No relevant systemic symptoms · the front of the torso is involved · FST II · the lesion is described as raised or bumpy · present for less than one week · male patient, age 18–29 · the patient described the issue as a rash · an image taken at an angle.
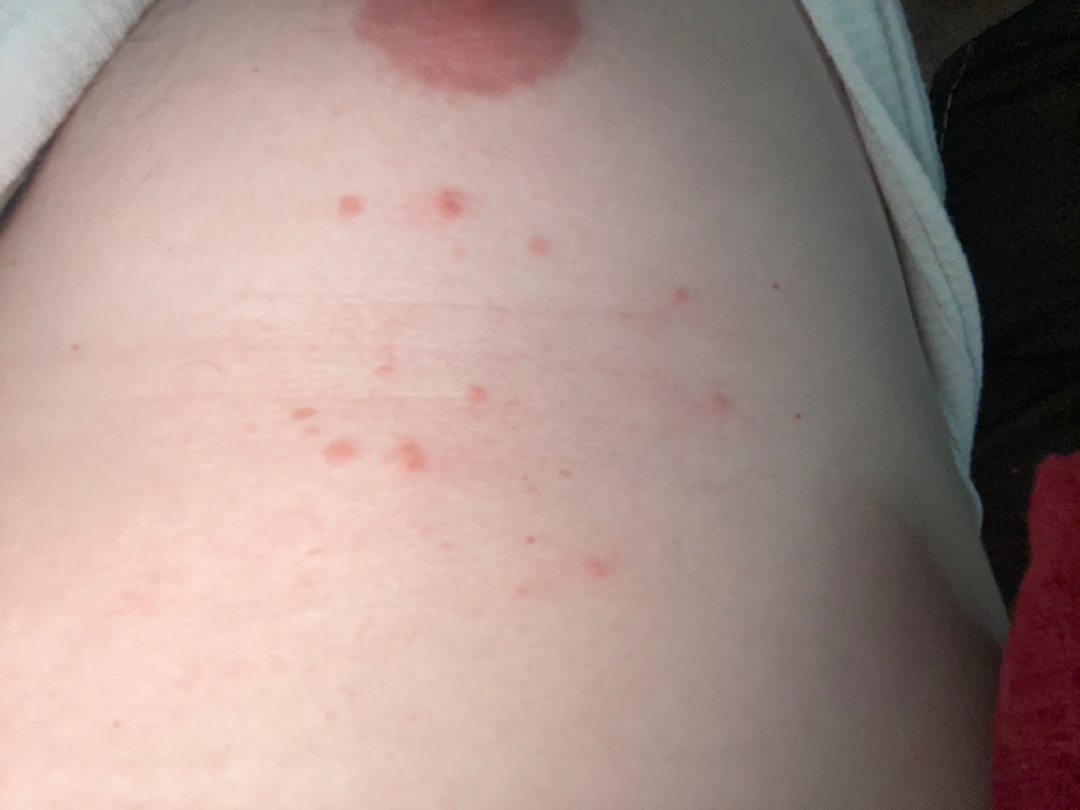| field | value |
|---|---|
| assessment | reviewed remotely by three dermatologists: the favored diagnosis is Folliculitis; also on the differential is Acne; also raised was Acute dermatitis, NOS; less likely is Grover's disease; a remote consideration is Irritant Contact Dermatitis; less probable is Insect Bite |